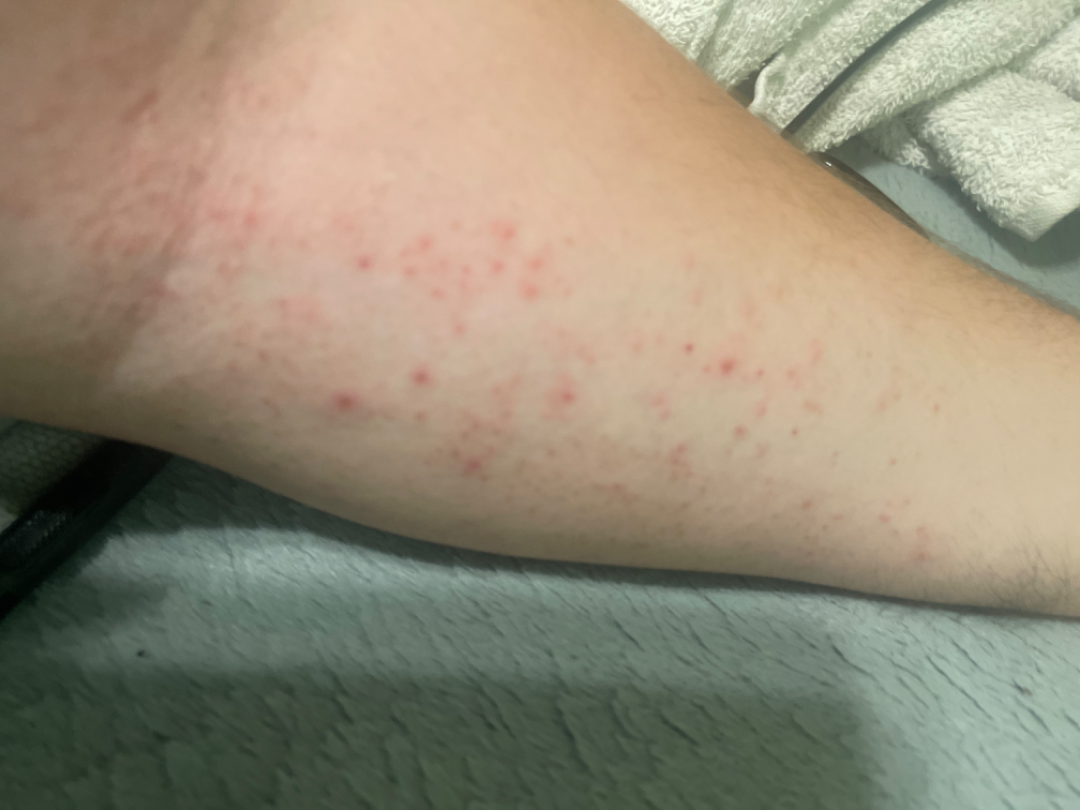A close-up photograph.
Reported lesion symptoms include itching.
The condition has been present for one to four weeks.
Self-categorized by the patient as a rash.
The lesion is described as raised or bumpy.
The arm is involved.
Eczema (primary).